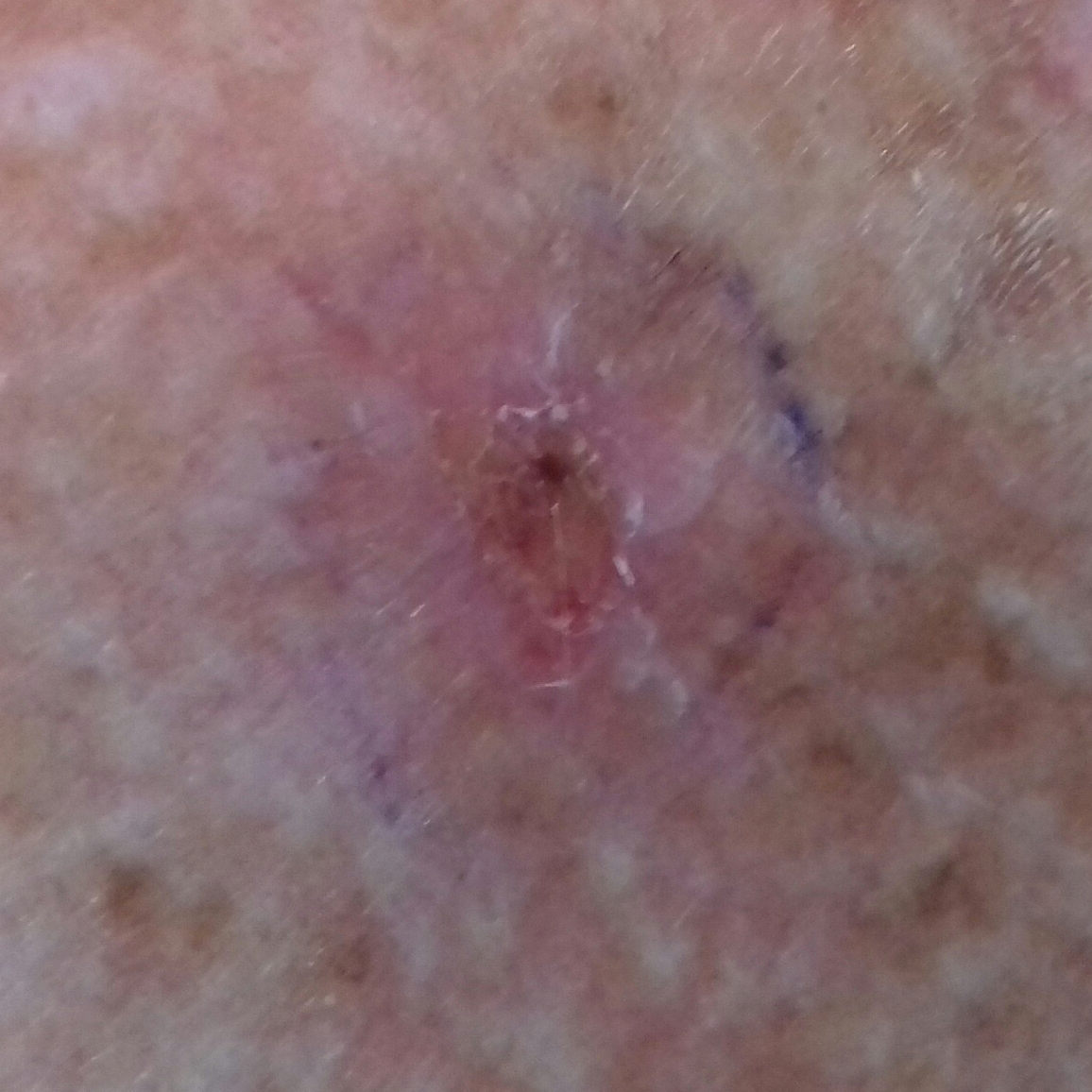Case summary:
Fitzpatrick II. A male patient in their 60s. A smartphone photograph of a skin lesion. The chart records pesticide exposure and prior skin cancer (patient or family). The lesion was found on the chest. The lesion measures 6 × 4 mm.
Diagnosis:
Histopathology confirmed a malignant skin lesion — a basal cell carcinoma.